The patient says their skin tans without first burning; a female patient 84 years old; acquired for a research image collection, with no referral diagnosis; a macroscopic clinical photograph of a skin lesion; the patient reports a personal history of cancer; few moles overall by the patient's own estimate: 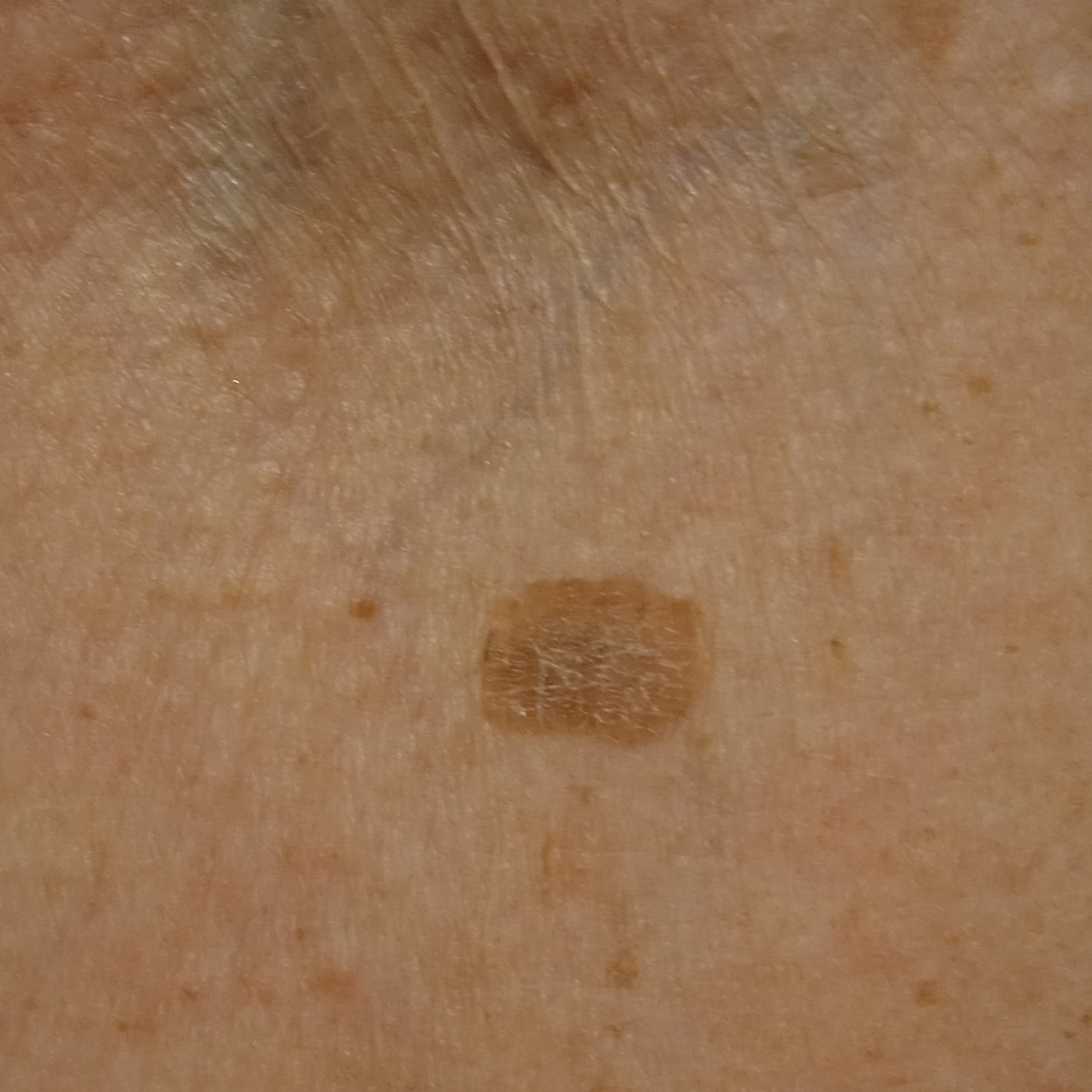Located on an arm. Measuring roughly 11.2 mm. Dermatologist review favored a seborrheic keratosis.